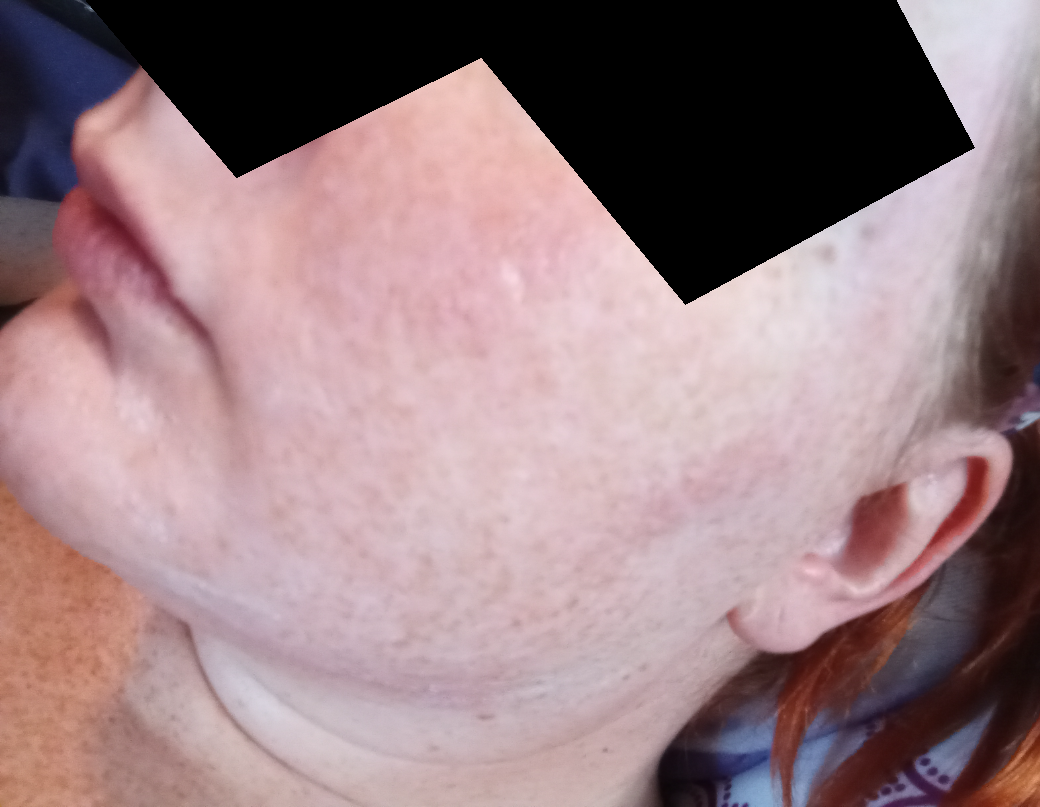Assessment:
On independent review by the dermatologists, Rosacea (1.00).